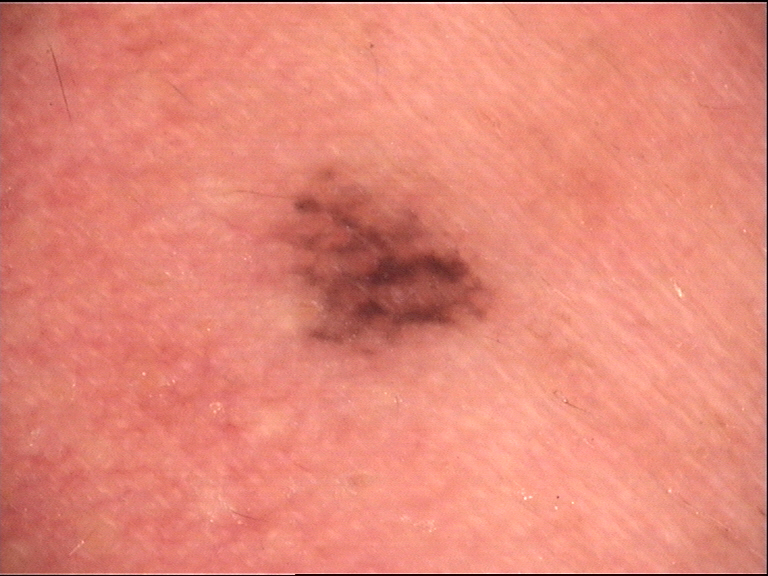A skin lesion imaged with a dermatoscope. The diagnostic label was a dysplastic junctional nevus.